A dermoscopy image of a single skin lesion.
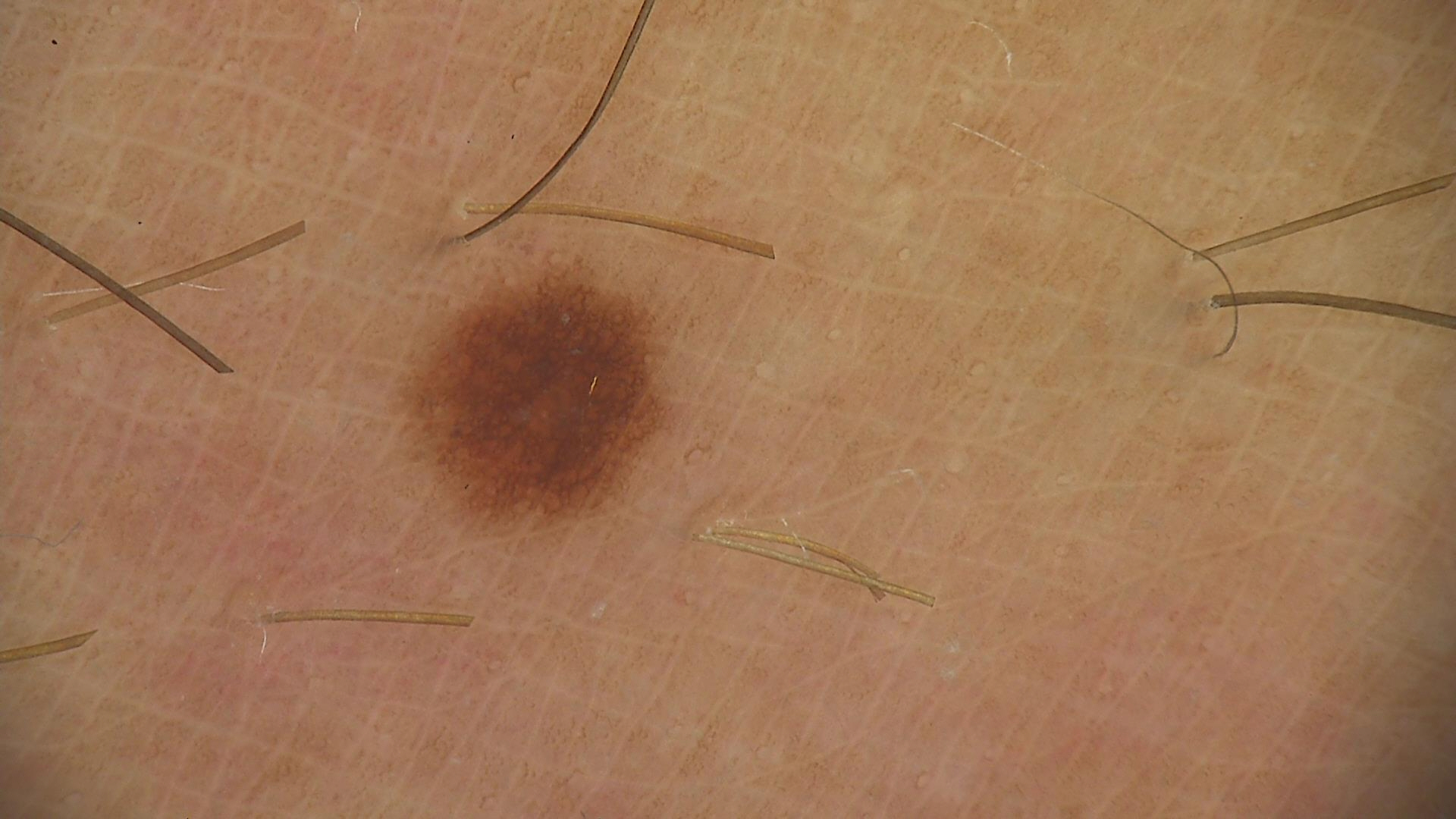Q: What is the lesion category?
A: banal
Q: What is the diagnosis?
A: junctional nevus (expert consensus)